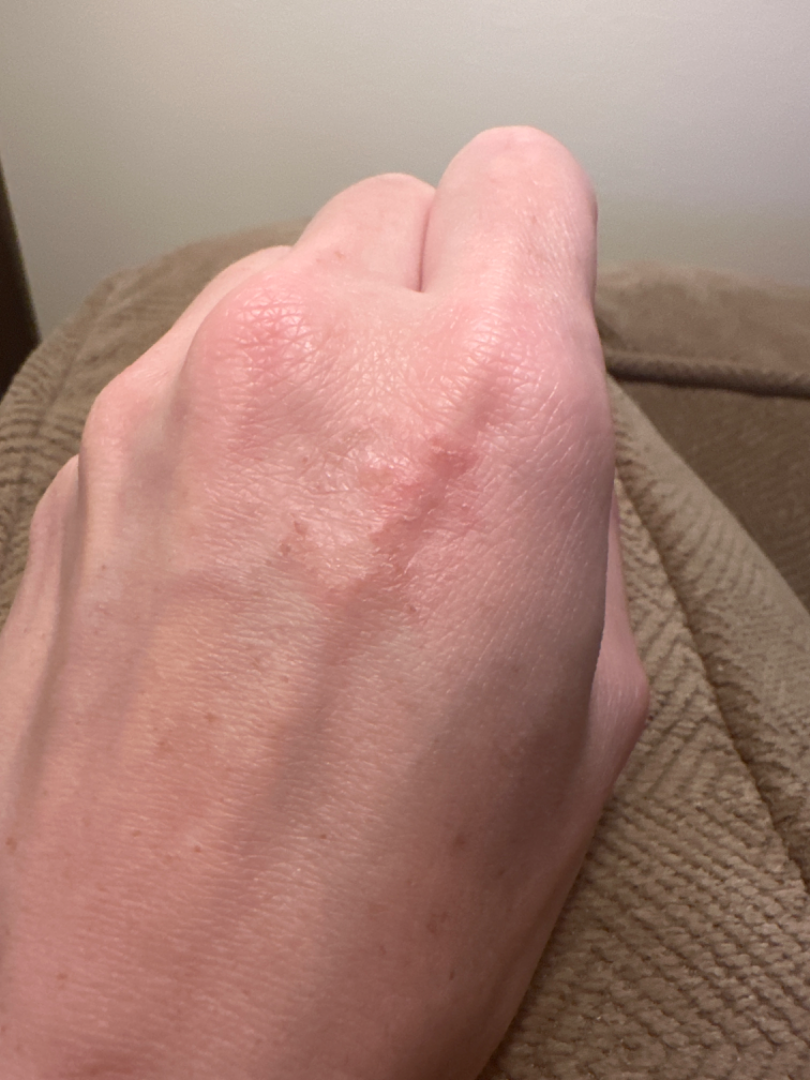The photograph is a close-up of the affected area.
Located on the back of the hand.
The patient considered this a rash.
Present for one to three months.
Female contributor, age 30–39.
On photographic review: favoring Granuloma annulare; an alternative is Eczema; lower on the differential is Tinea.